Skin tone: Fitzpatrick III; the contributor is a male aged 50–59; this image was taken at an angle; the arm is involved; the patient considered this a rash; texture is reported as raised or bumpy and rough or flaky; reported duration is more than one year: 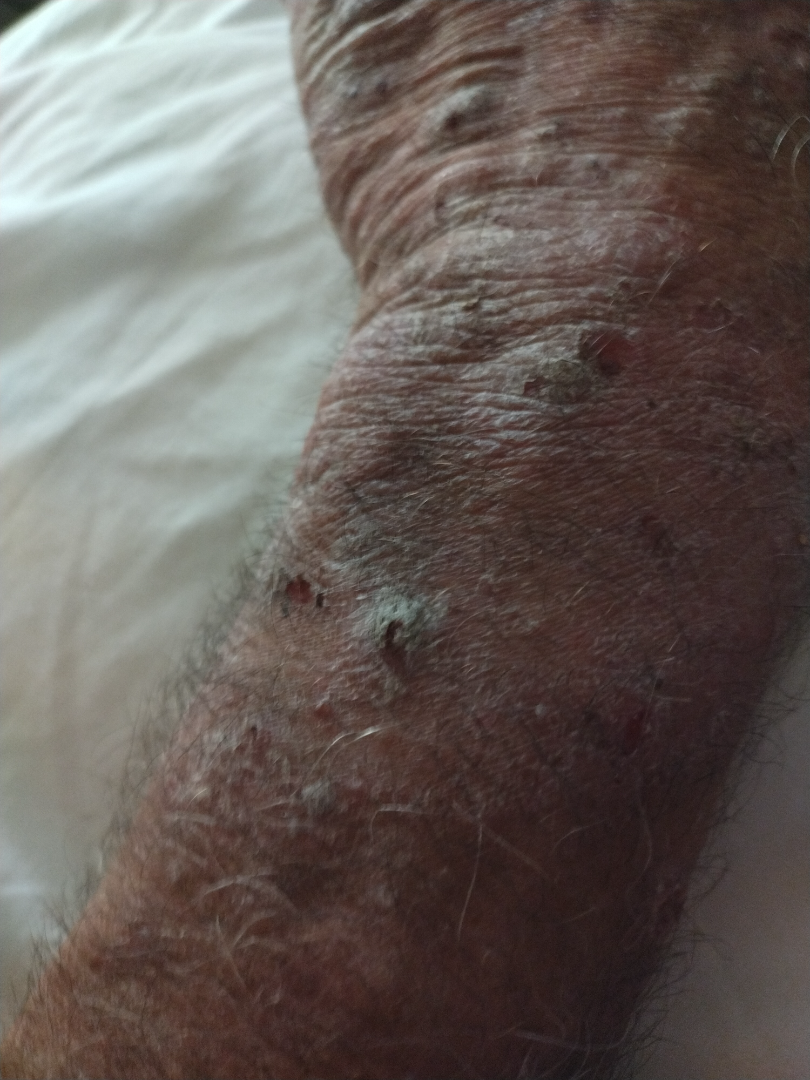On photographic review, the differential, in no particular order, includes Prurigo nodularis and Actinic Keratosis.